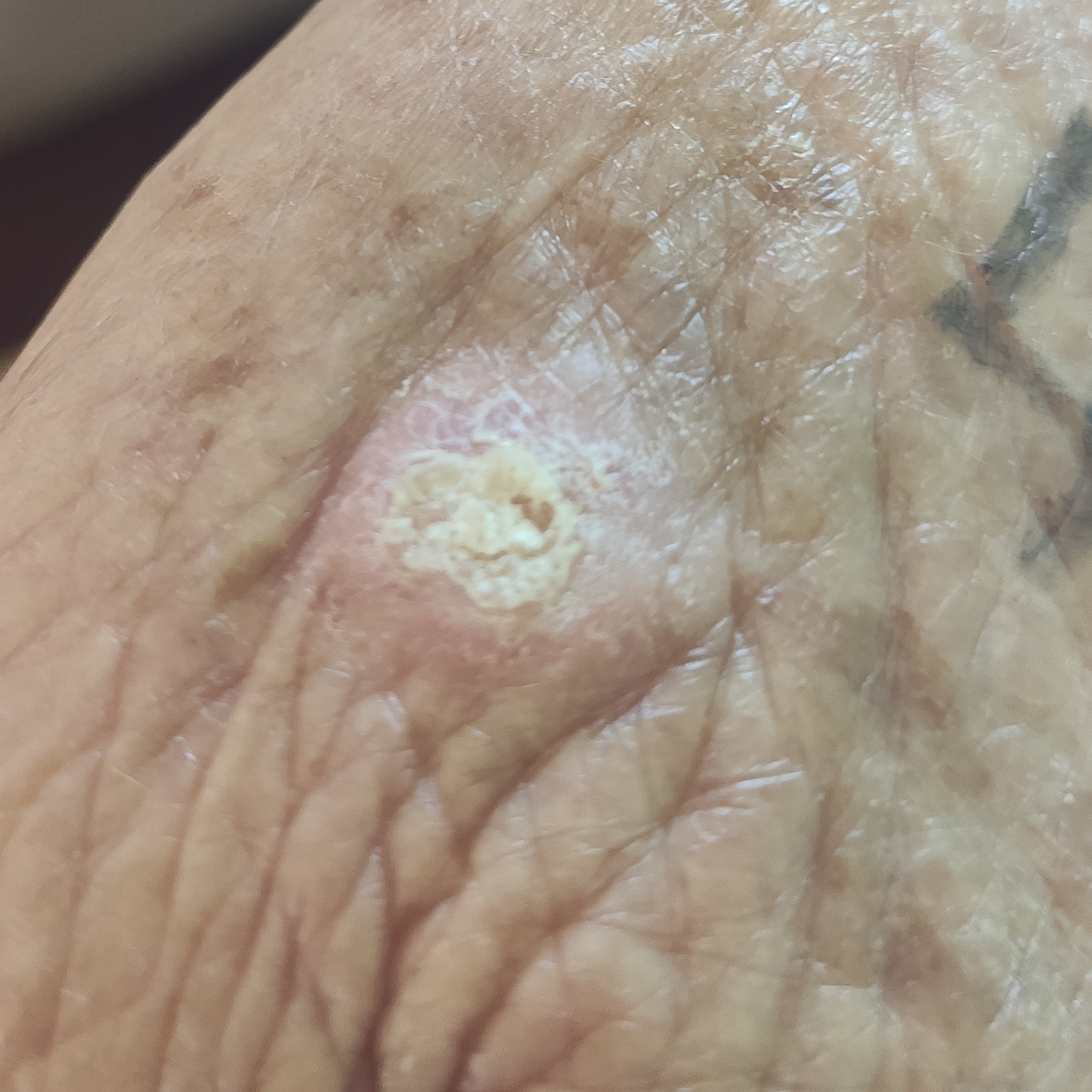A female patient in their 70s.
Skin type III.
The lesion involves a hand.
The lesion measures 10 × 7 mm.
Histopathology confirmed an actinic keratosis.